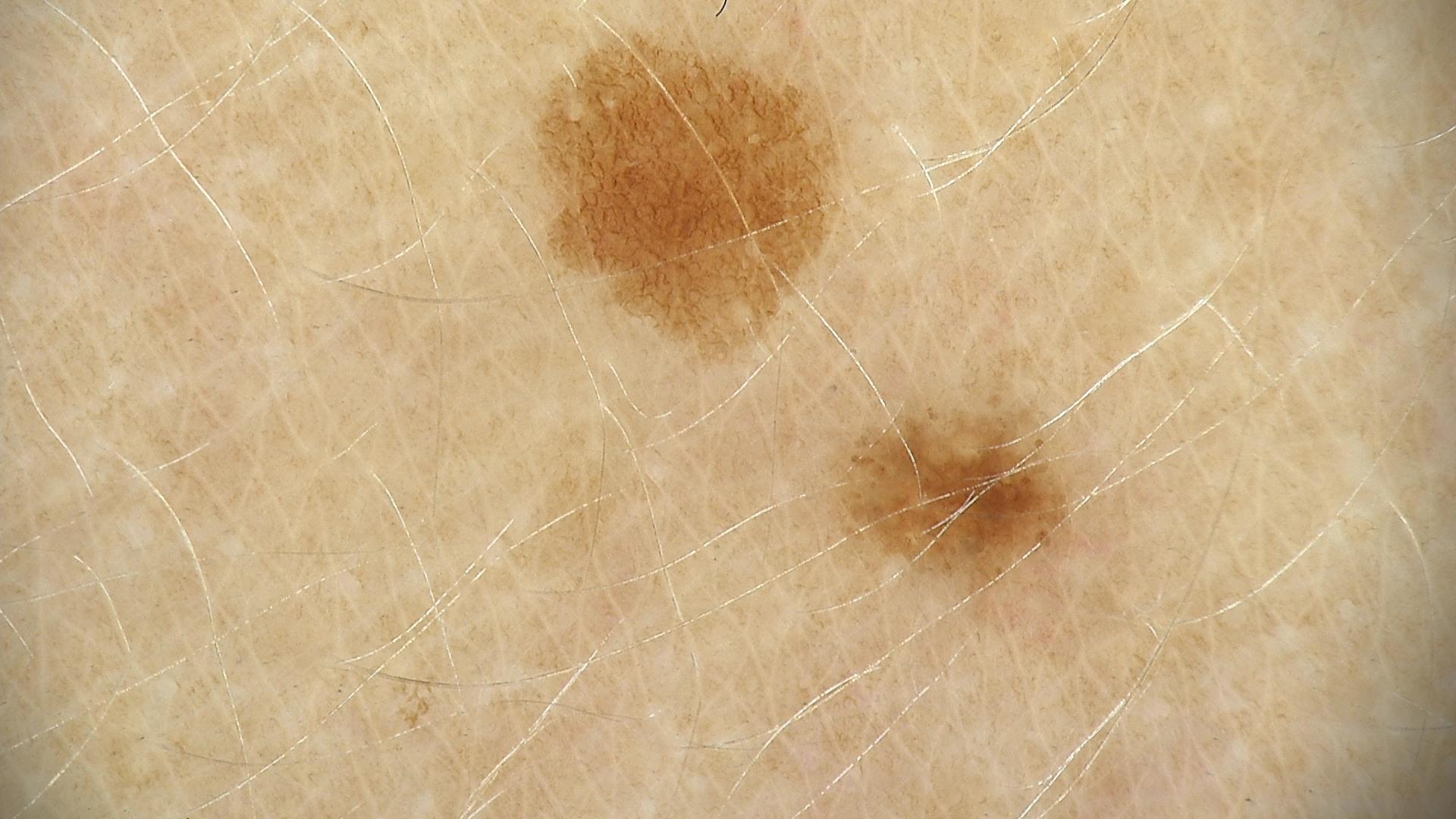{"diagnosis": {"name": "dysplastic junctional nevus", "code": "jd", "malignancy": "benign", "super_class": "melanocytic", "confirmation": "expert consensus"}}